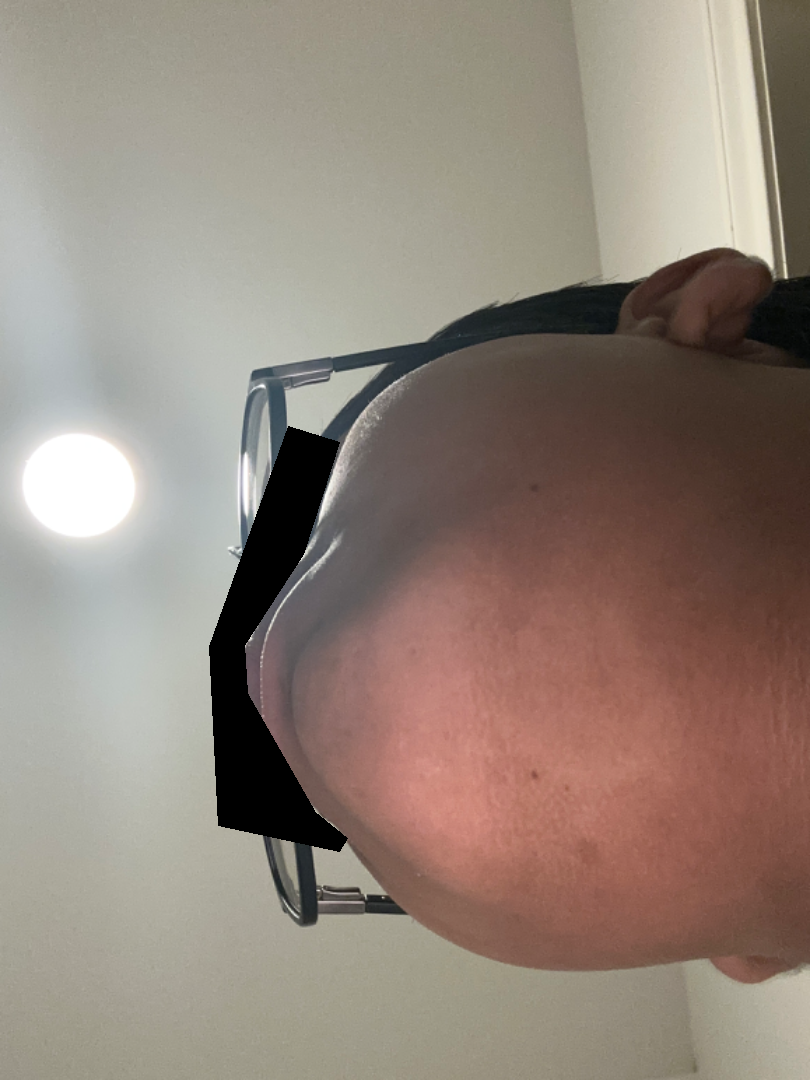Review:
The dermatologist could not determine a likely condition from the photograph alone.